The subject is a male aged around 45, a dermoscopy image of a single skin lesion: 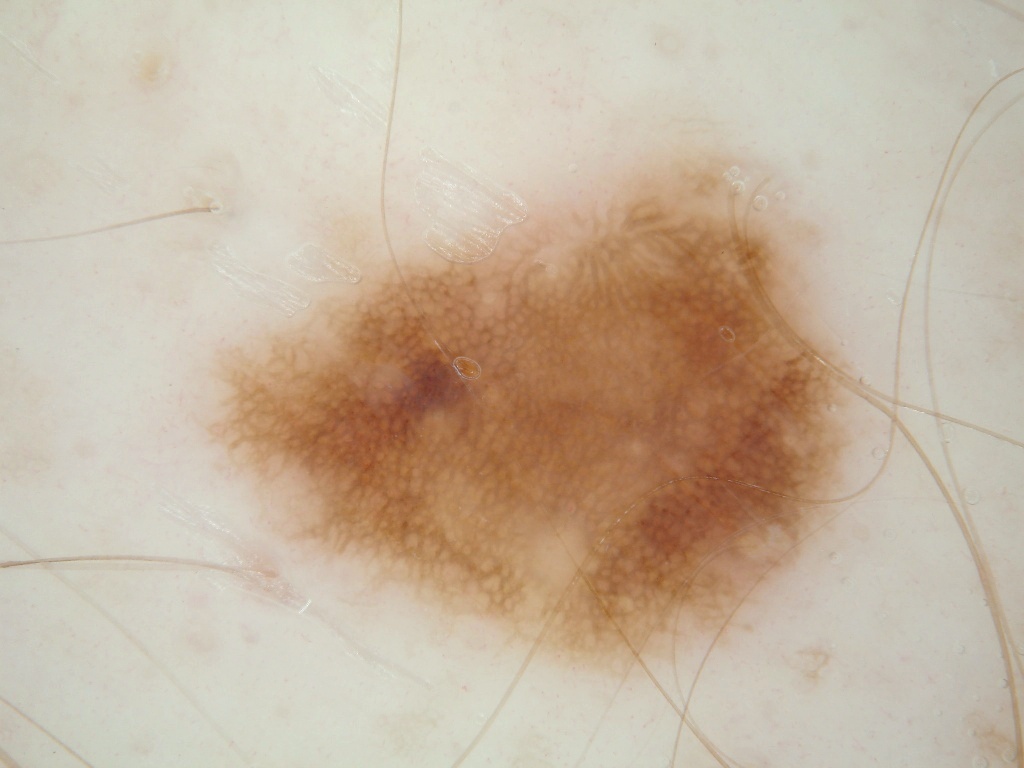Case summary:
In (x1, y1, x2, y2) order, the lesion occupies the region (220, 157, 869, 664). Dermoscopic review identifies pigment network; no negative network, milia-like cysts, streaks, or globules. The lesion covers approximately 27% of the dermoscopic field.
Conclusion:
The diagnostic assessment was a melanocytic nevus, a benign skin lesion.